This is a close-up image, the lesion involves the top or side of the foot: 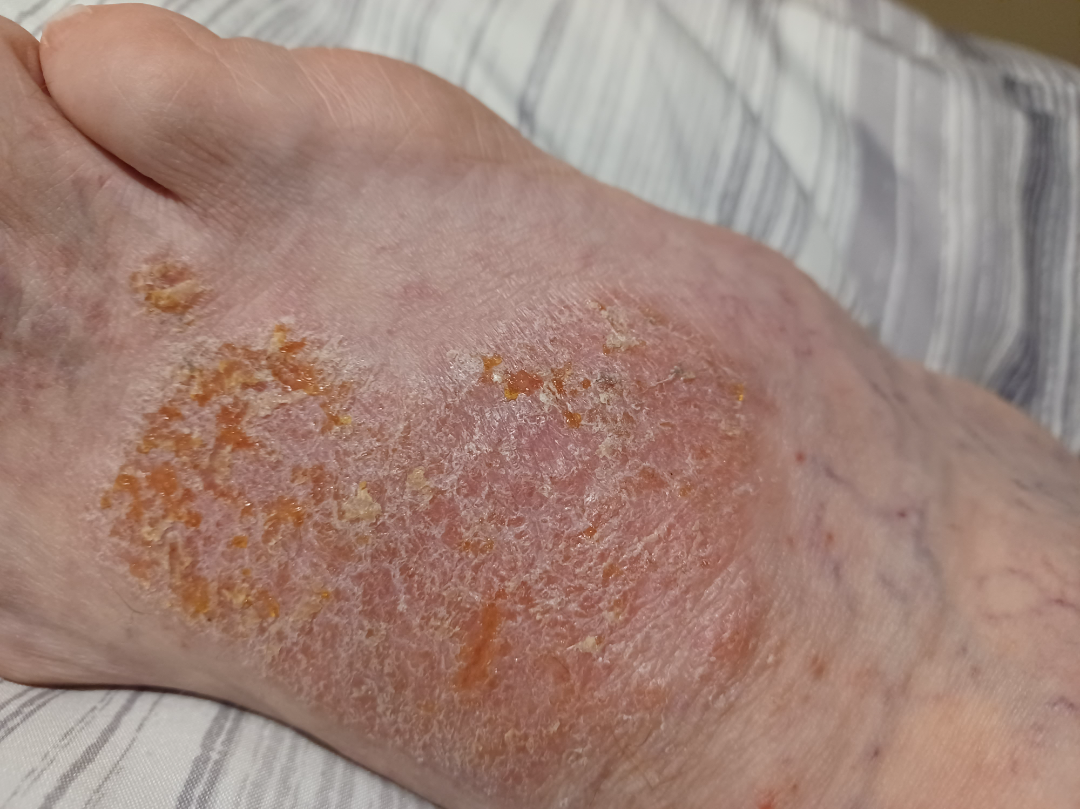The patient considered this a rash.
The contributor notes darkening, itching, bothersome appearance, burning, pain, enlargement and bleeding.
The condition has been present for three to twelve months.
The lesion is described as flat, fluid-filled and rough or flaky.
On dermatologist assessment of the image: favoring Allergic Contact Dermatitis; possibly Impetigo; also consider Irritant Contact Dermatitis.